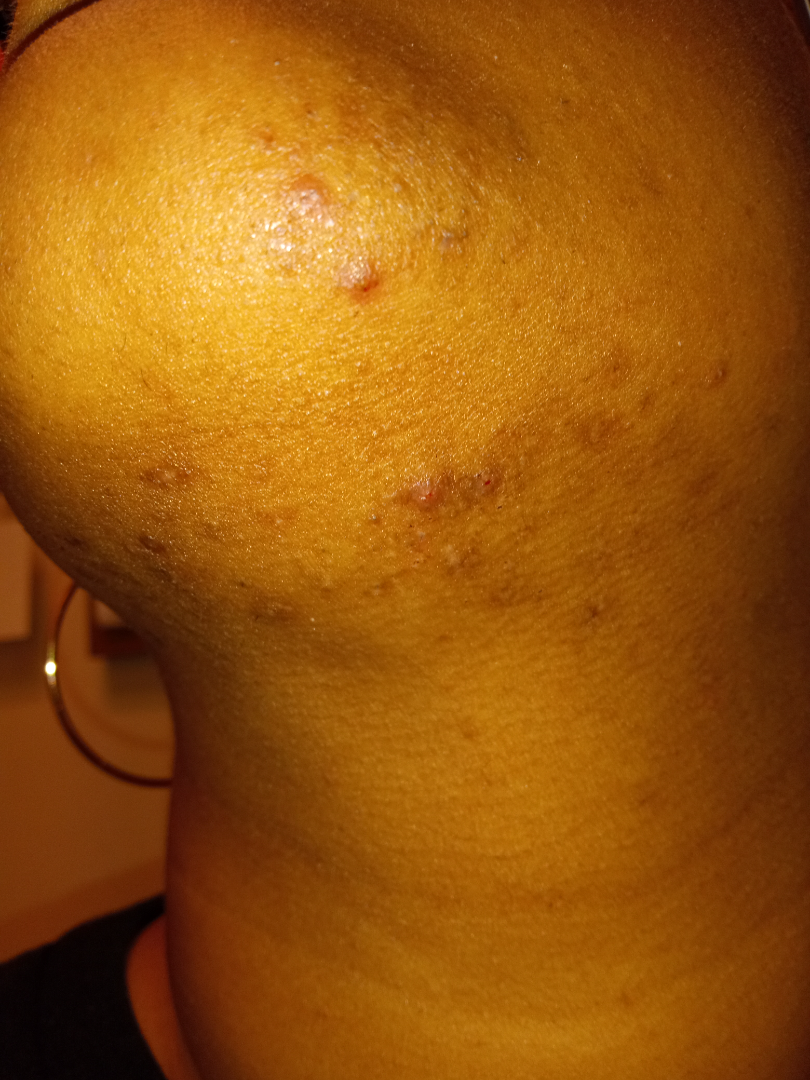Present for one to three months. The contributor reports the lesion is fluid-filled and raised or bumpy. The patient did not report lesion symptoms. FST V. The patient considered this acne. This is a close-up image. Located on the head or neck. No constitutional symptoms were reported. Most consistent with Acne.